A clinical photograph showing a skin lesion in context · the patient is Fitzpatrick phototype III · a male patient roughly 70 years of age:
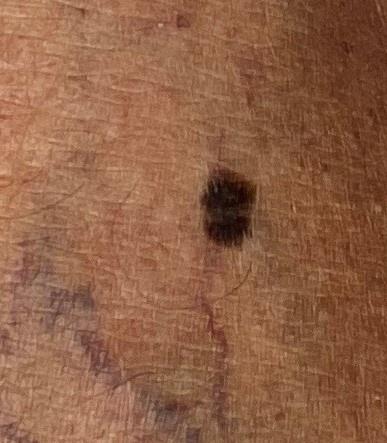body site = a lower extremity | diagnostic label = Nevus (biopsy-proven).